The affected area is the head or neck; close-up view:
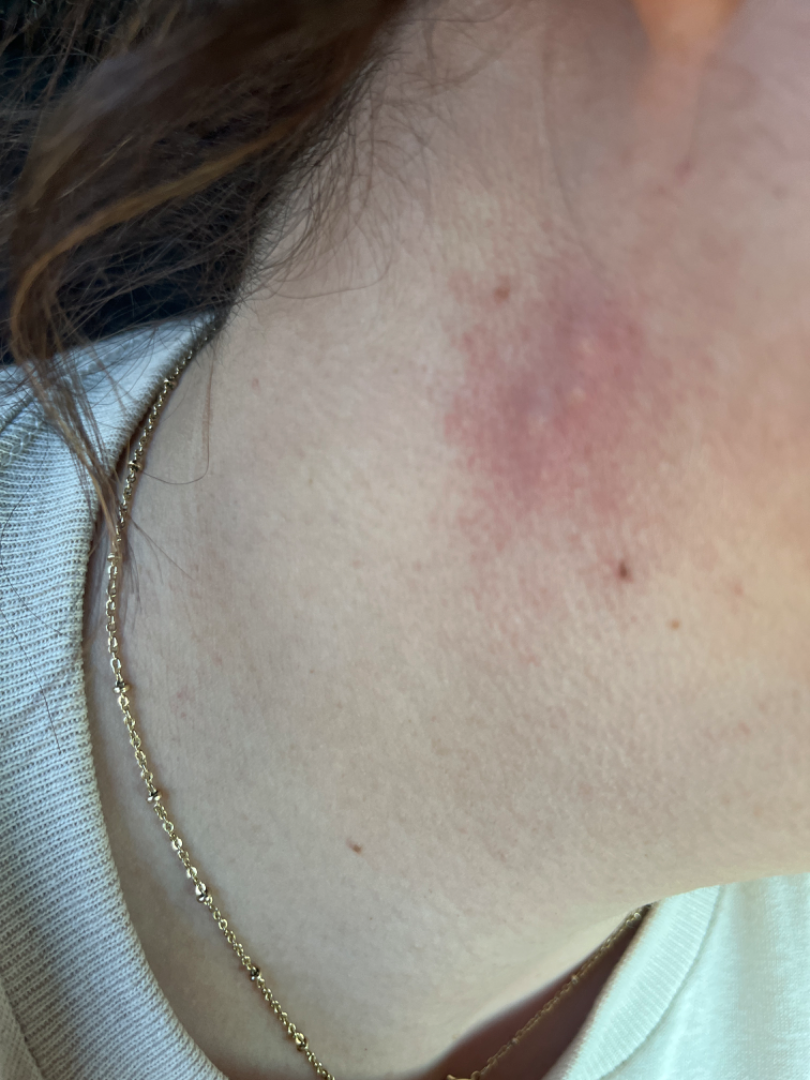History: The lesion is described as raised or bumpy. Reported duration is less than one week. Impression: On photographic review by a dermatologist, most consistent with Insect Bite; also raised was Acne; possibly Allergic Contact Dermatitis.